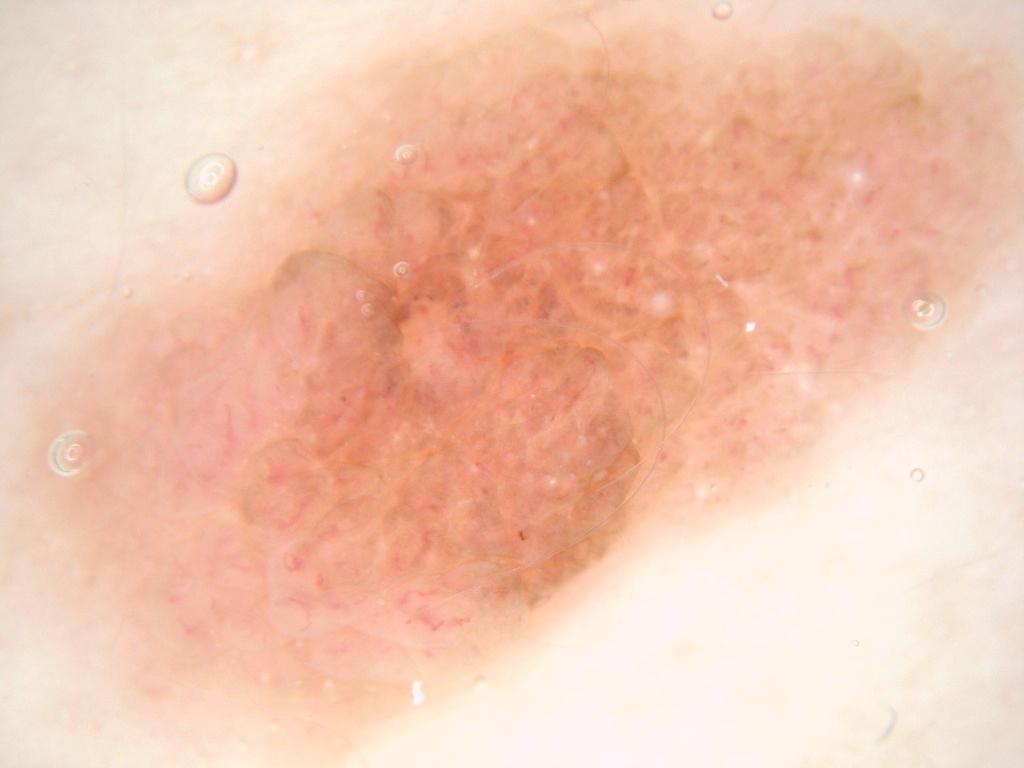<record>
  <patient>
    <sex>male</sex>
    <age_approx>20</age_approx>
  </patient>
  <image>
    <modality>dermoscopy</modality>
  </image>
  <lesion_location>spans the dermoscopic field</lesion_location>
  <dermoscopic_features>
    <present>milia-like cysts</present>
    <absent>streaks, negative network, pigment network</absent>
  </dermoscopic_features>
  <diagnosis>
    <name>melanocytic nevus</name>
    <malignancy>benign</malignancy>
    <lineage>melanocytic</lineage>
    <provenance>clinical</provenance>
  </diagnosis>
</record>